A female patient age 62; history notes prior skin cancer (patient or family), prior malignancy (patient or family), tobacco use, no alcohol use, and no pesticide exposure; a clinical close-up photograph of a skin lesion; the patient is Fitzpatrick II.
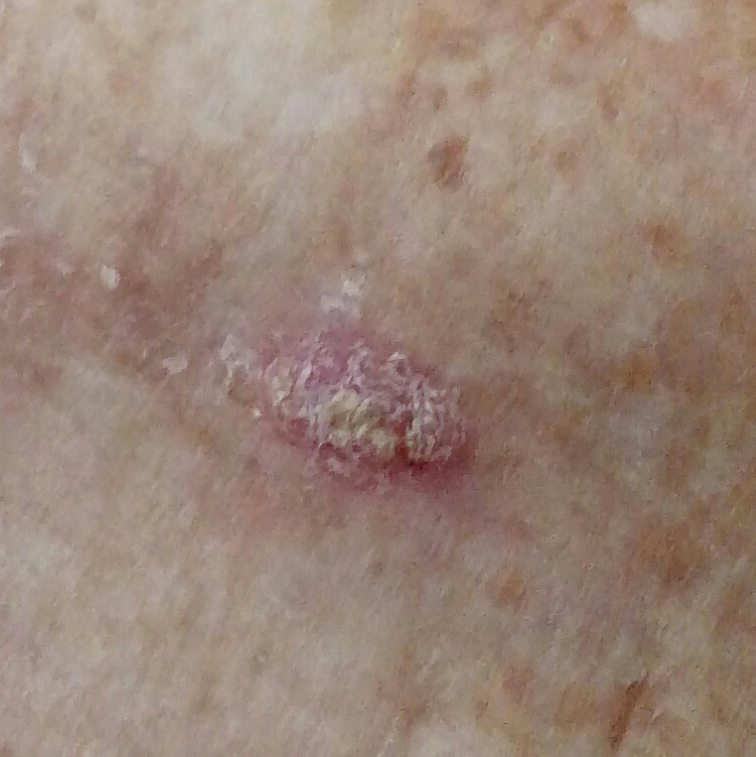{
  "lesion_location": "the chest",
  "lesion_size": {
    "diameter_1_mm": 11.0,
    "diameter_2_mm": 6.0
  },
  "symptoms": {
    "present": [
      "growth",
      "itching",
      "elevation",
      "bleeding"
    ],
    "absent": [
      "change in appearance",
      "pain"
    ]
  },
  "diagnosis": {
    "name": "squamous cell carcinoma",
    "code": "SCC",
    "malignancy": "malignant",
    "confirmation": "histopathology"
  }
}